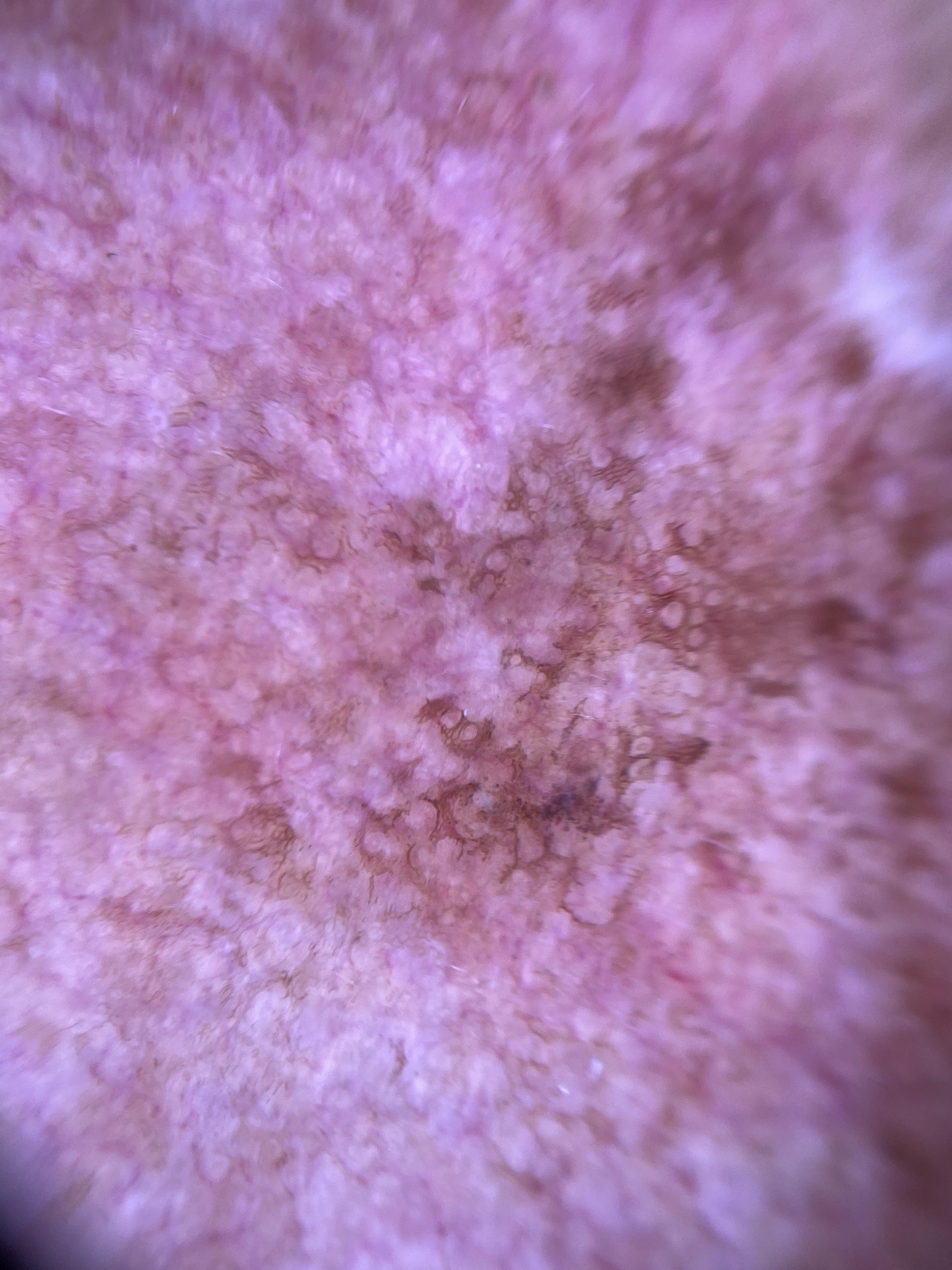Q: How was this image acquired?
A: contact-polarized dermoscopy
Q: What does the history note?
A: a previous melanoma
Q: Where on the body is the lesion?
A: the head or neck
Q: What did the workup show?
A: Melanoma (biopsy-proven)